A skin lesion imaged with a dermatoscope: 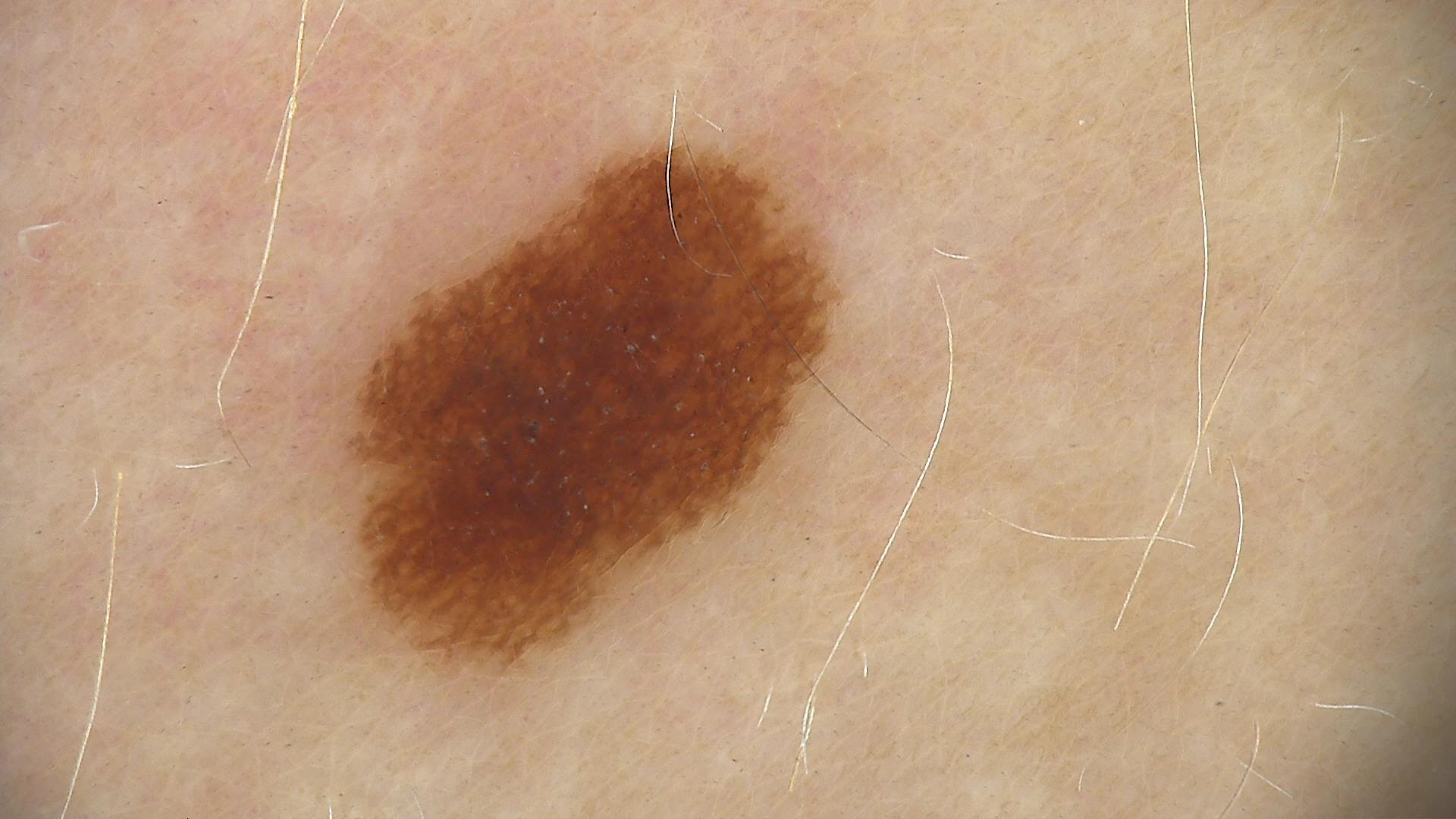The diagnosis was a dysplastic junctional nevus.